A dermoscopic image of a skin lesion. The subject is a male aged around 55 — 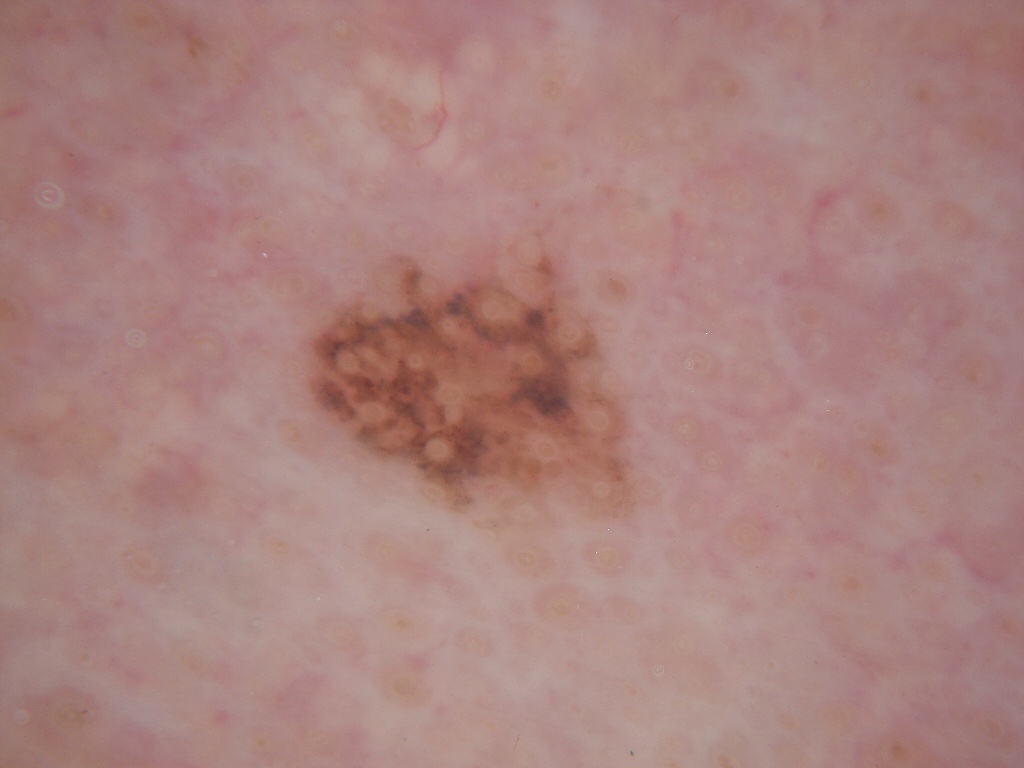{
  "lesion_location": {
    "bbox_xyxy": [
      285,
      223,
      650,
      561
    ]
  },
  "dermoscopic_features": {
    "present": [],
    "absent": [
      "globules",
      "streaks",
      "pigment network",
      "negative network",
      "milia-like cysts"
    ]
  },
  "diagnosis": {
    "name": "melanocytic nevus",
    "malignancy": "benign",
    "lineage": "melanocytic",
    "provenance": "clinical"
  }
}